The patient says their skin tans without first burning · a dermoscopic image of a skin lesion · a moderate number of moles by the patient's own estimate · by self-report, a personal history of cancer, no family history of skin cancer, and no sunbed use · a male patient 54 years old · collected as part of a research study, without a referral diagnosis — 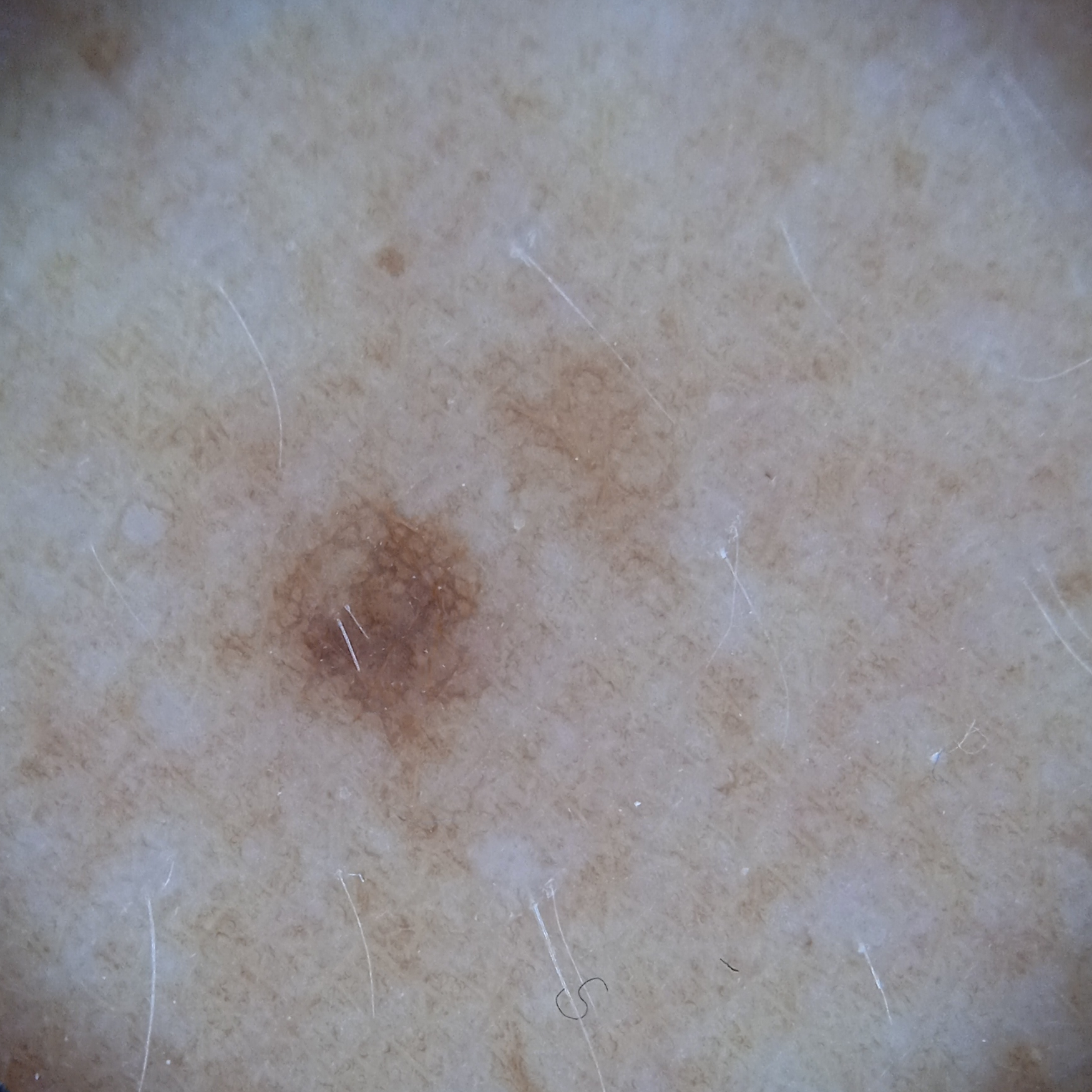The lesion involves an arm.
Measuring roughly 2.9 mm.
The diagnostic impression was a melanocytic nevus.